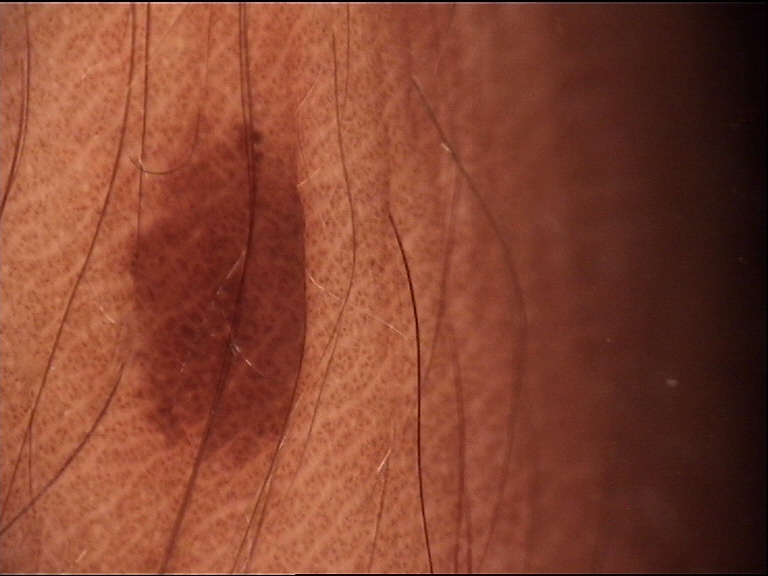Diagnosed as a junctional nevus.